This is a dermoscopic photograph of a skin lesion; a female subject aged 58 to 62.
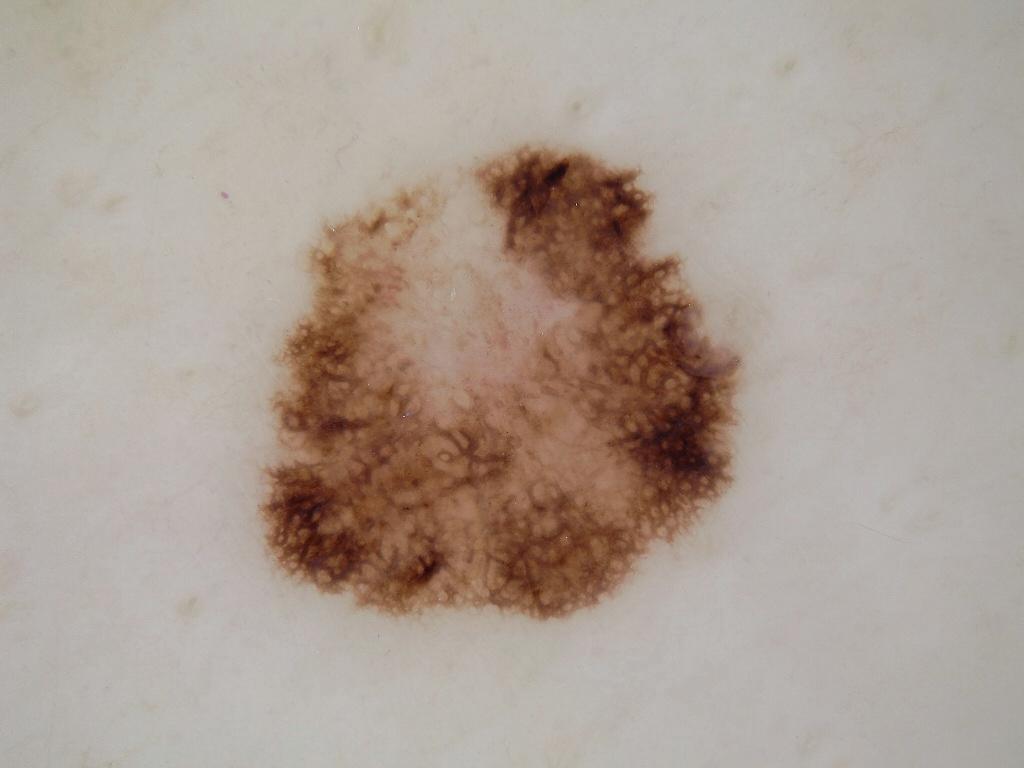The lesion takes up about 25% of the image. Lesion location: box(246, 134, 759, 630). Dermoscopic review identifies pigment network and globules, with no streaks, negative network, or milia-like cysts. Histopathology confirmed a melanoma.